A dermoscopy image of a single skin lesion.
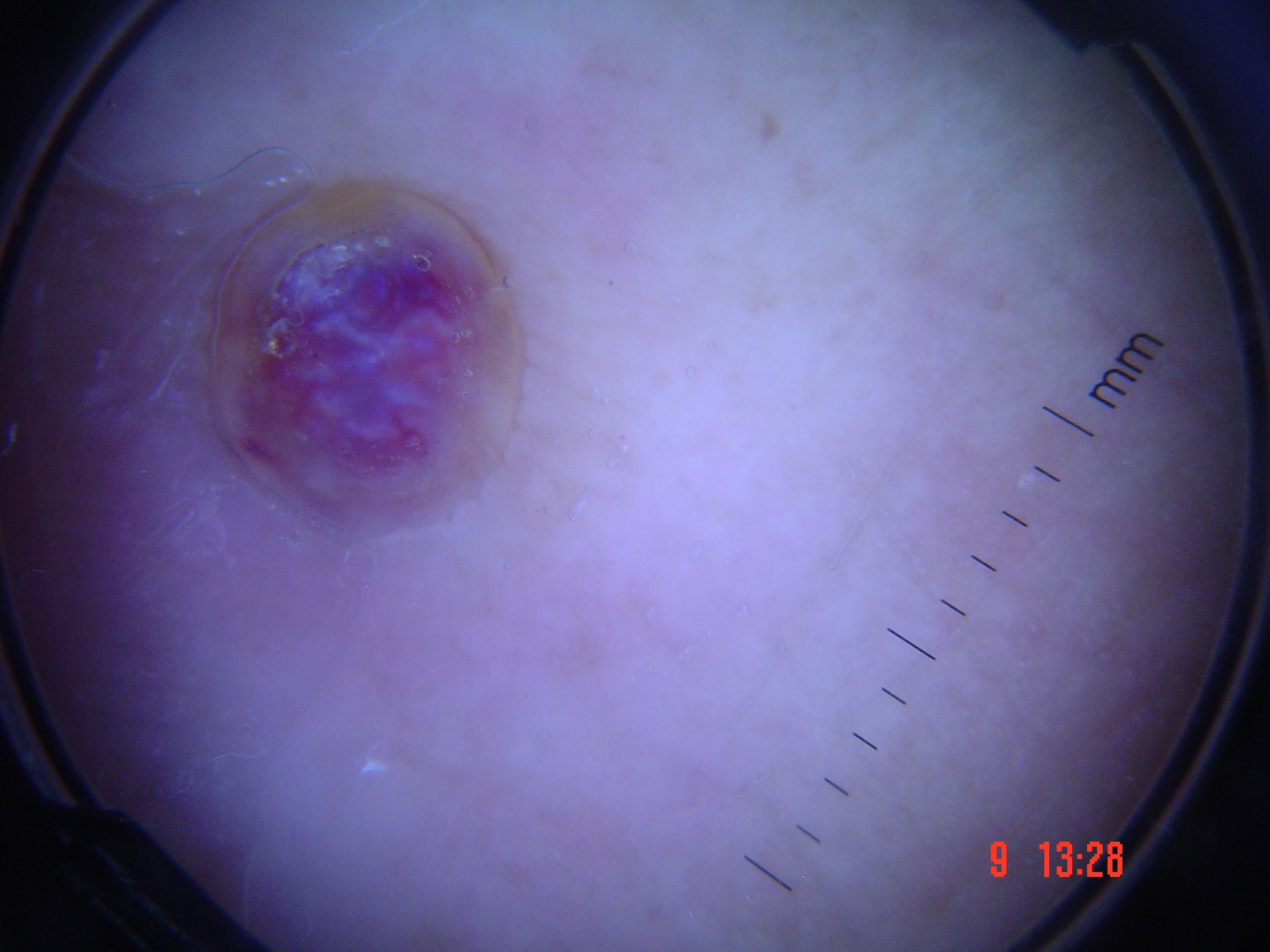Histopathologically confirmed as a vascular lesion — a Kaposi sarcoma.